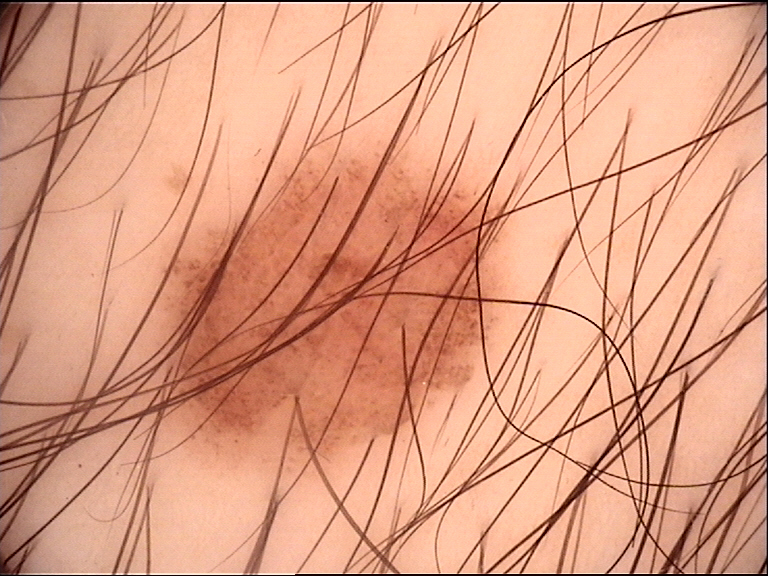  image: dermatoscopy
  lesion_type:
    main_class: banal
    pattern: junctional
  diagnosis:
    name: junctional nevus
    code: jb
    malignancy: benign
    super_class: melanocytic
    confirmation: expert consensus